An image taken at an angle:
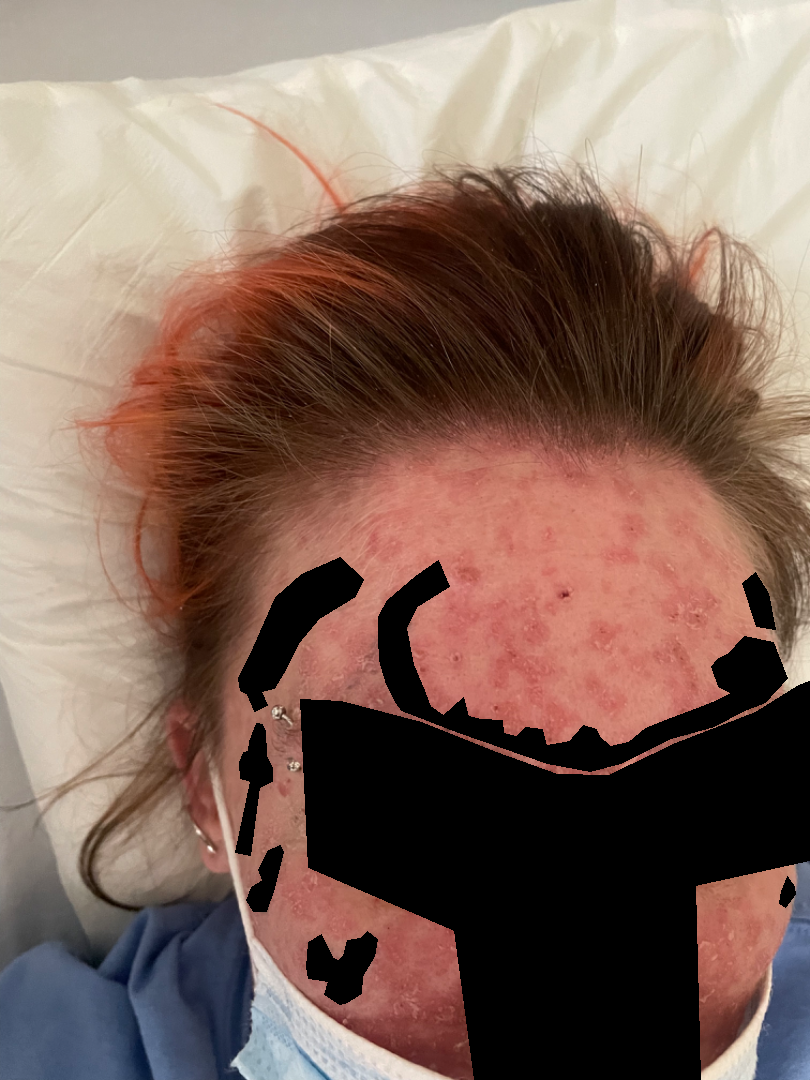assessment: indeterminate from the photograph